A male subject in their 70s · a clinical photograph showing a skin lesion · Fitzpatrick phototype II.
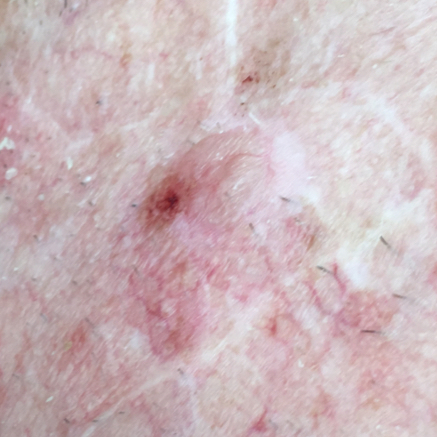Findings:
Measuring about 5 × 4 mm. The patient describes that the lesion is elevated, hurts, and itches.
Conclusion:
Histopathologically confirmed as a basal cell carcinoma.